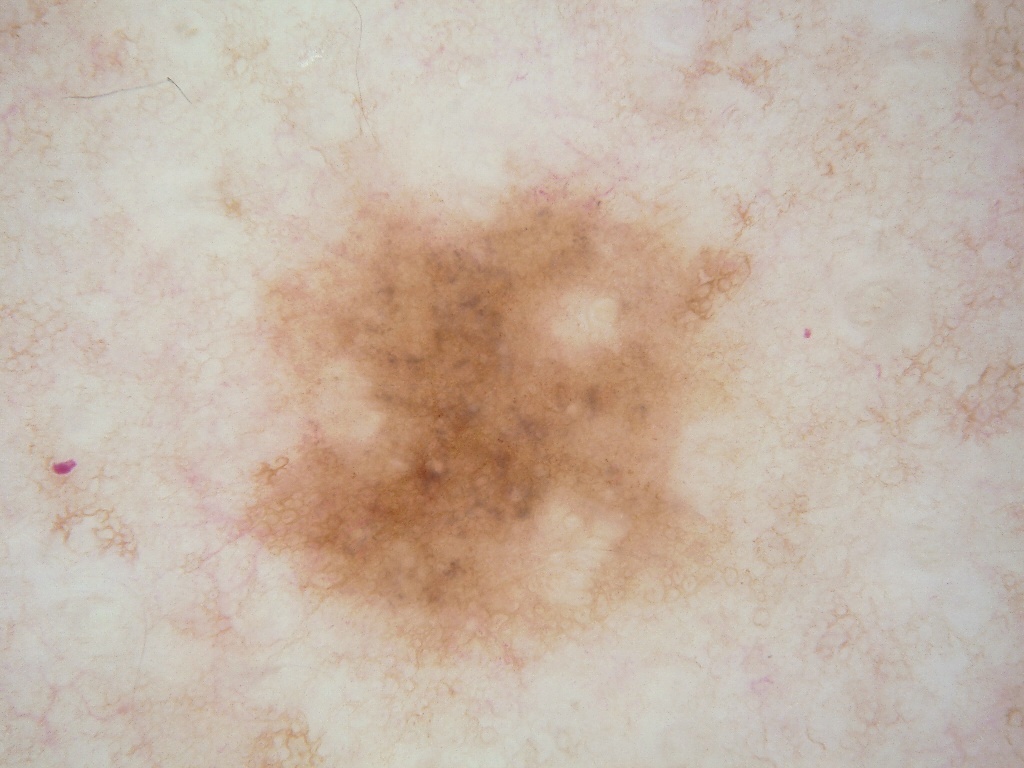The patient is a female aged around 45. A dermoscopic image of a skin lesion. The lesion spans box(212, 149, 817, 689). The lesion covers approximately 34% of the dermoscopic field. Dermoscopic review identifies pigment network; no milia-like cysts, streaks, globules, or negative network. Diagnosed as a melanocytic nevus.